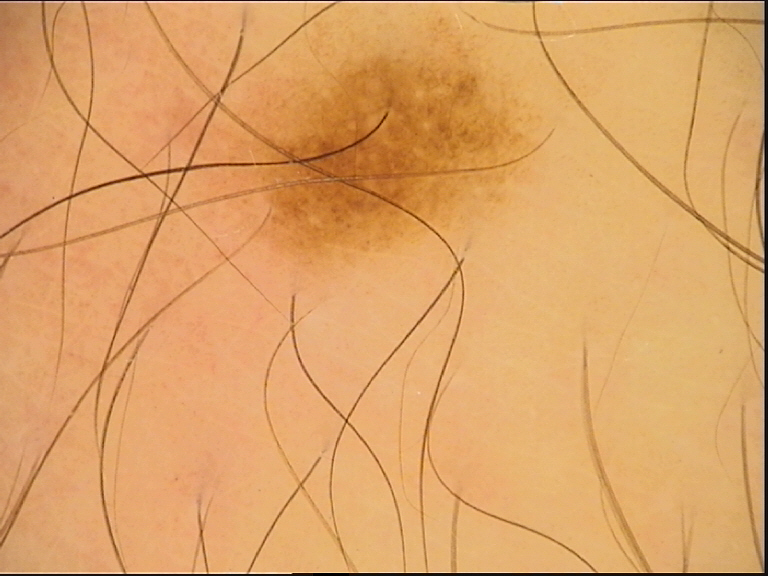image: dermoscopy
diagnostic label: dysplastic junctional nevus (expert consensus)